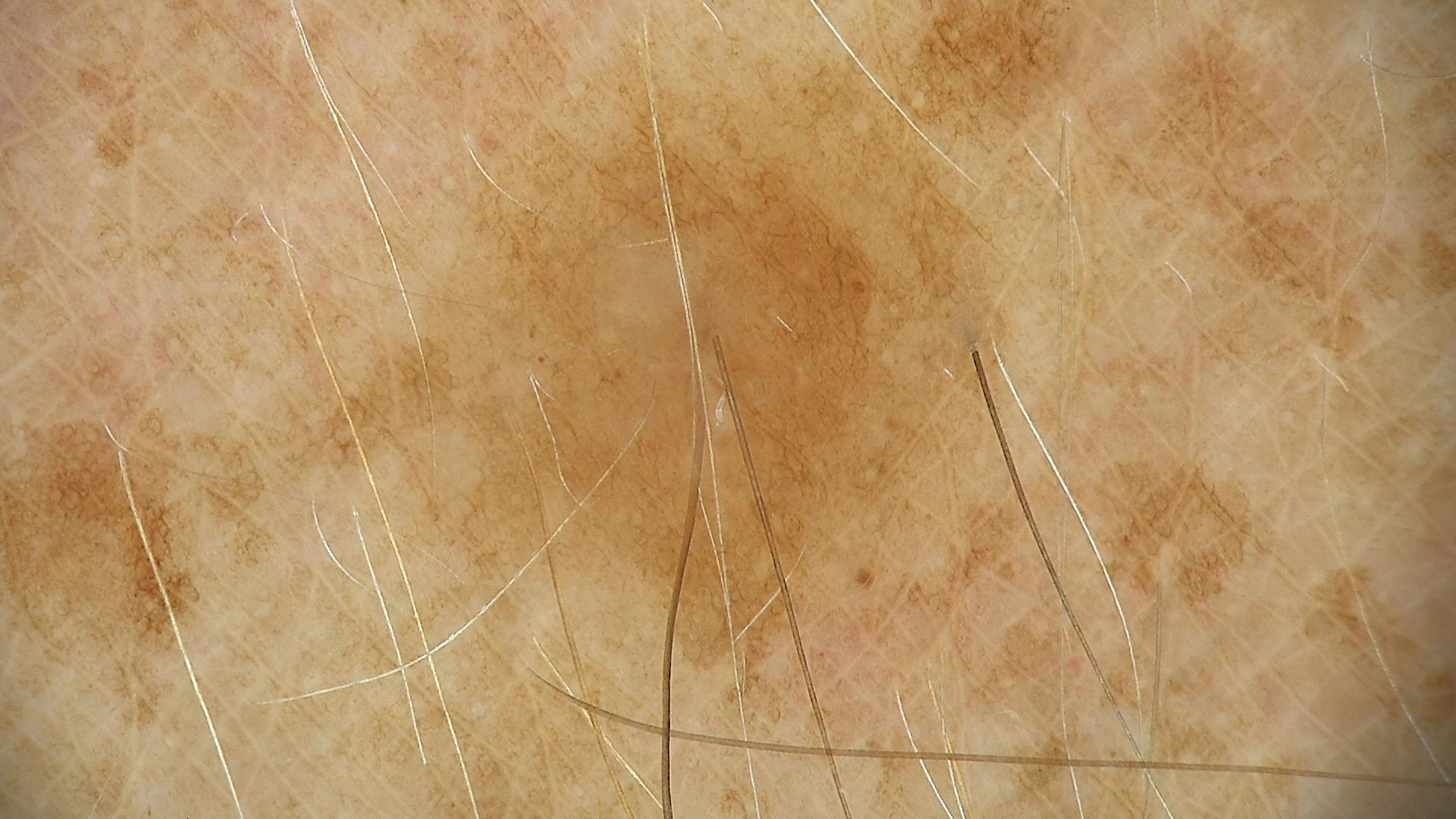Summary:
Dermoscopy of a skin lesion.
Impression:
Diagnosed as a benign lesion — a solar lentigo.